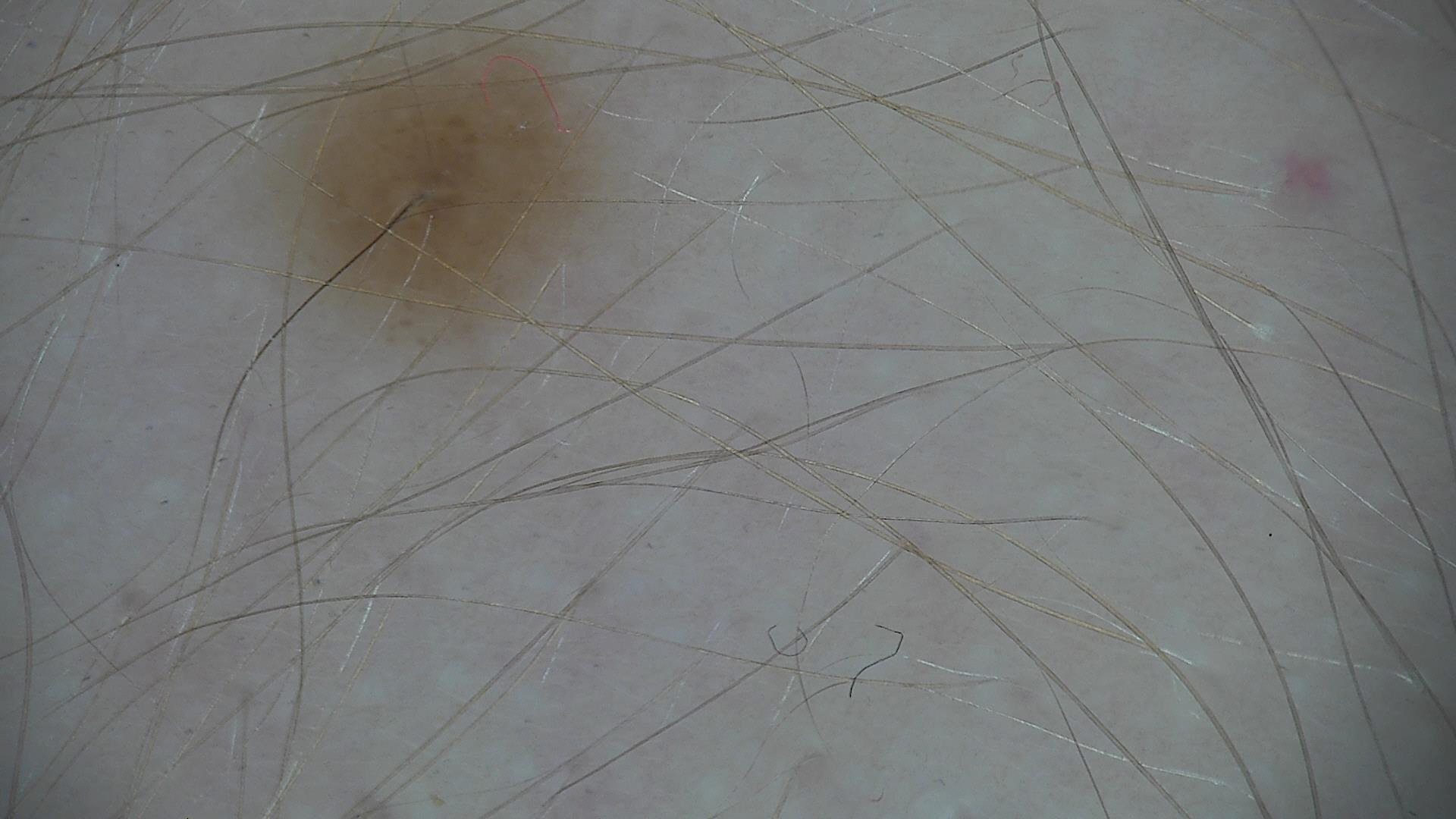The architecture is that of a banal lesion. The diagnostic label was a junctional nevus.